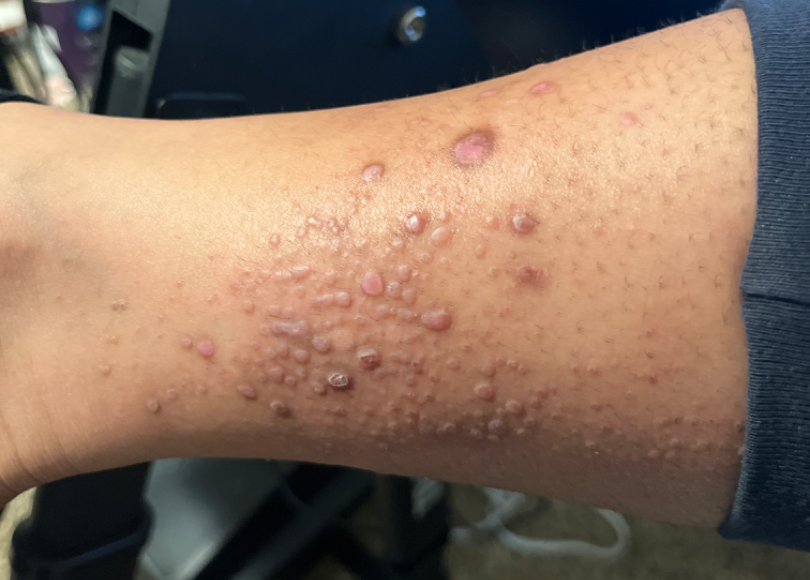framing=at a distance; symptoms=itching; body site=leg; surface texture=fluid-filled and raised or bumpy; dermatologist impression=the differential is split between Amyloidosis of skin, Pretibial myxedema and Lichen Simplex Chronicus.